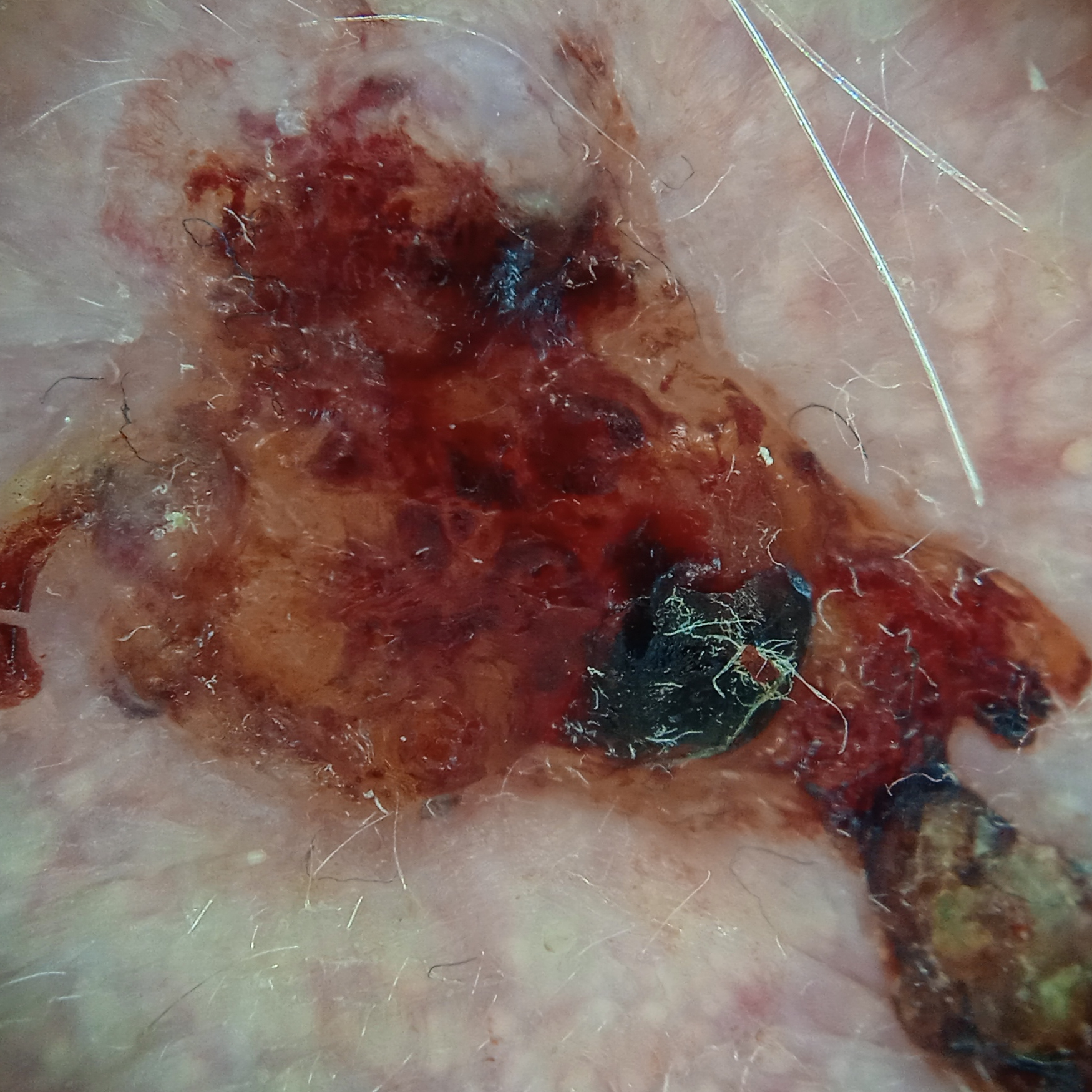Case:
– referral: clinical suspicion of basal cell carcinoma
– image type: dermoscopy
– subject: male, aged 89
– sun reaction: skin reddens painfully with sun exposure
– site: the face
– diagnosis: basal cell carcinoma (biopsy-proven)